A dermoscopic image of a skin lesion: 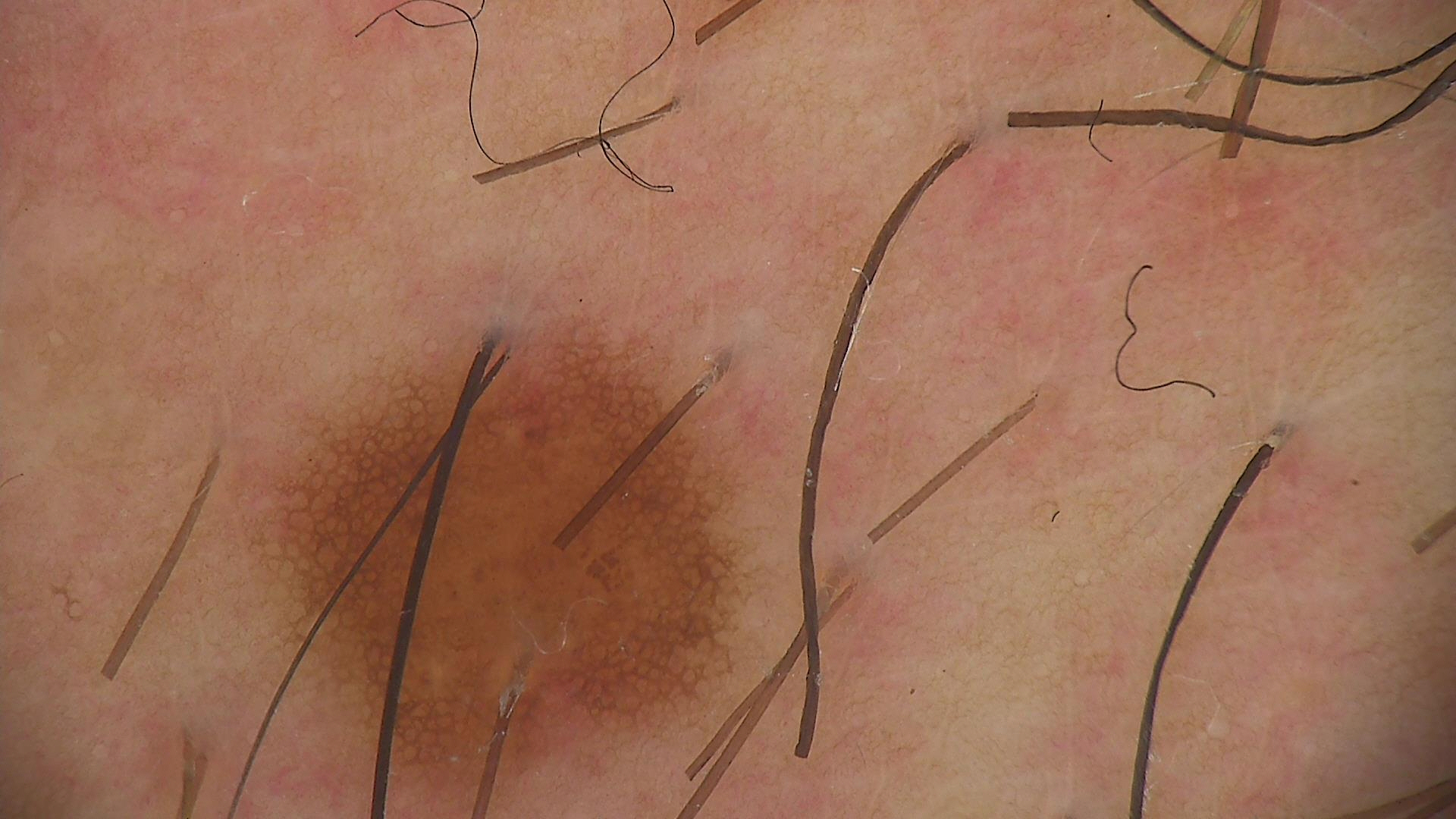assessment = dysplastic junctional nevus (expert consensus).